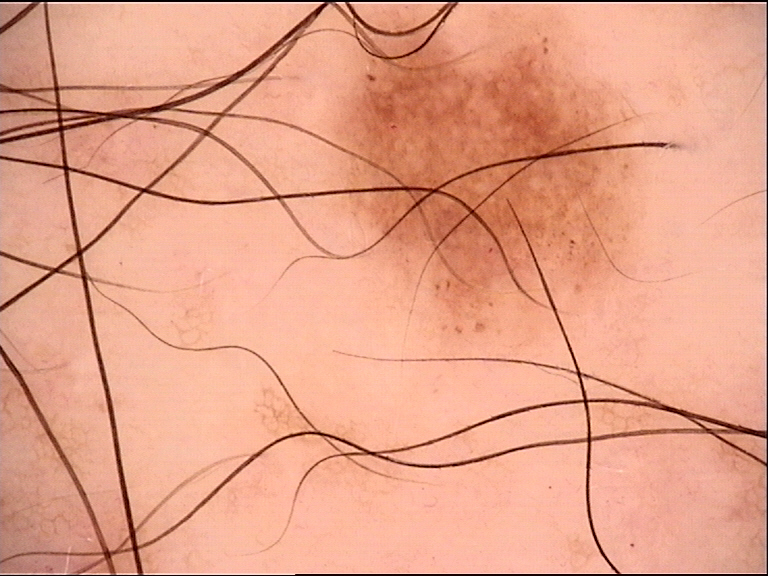Diagnosed as a dysplastic junctional nevus.